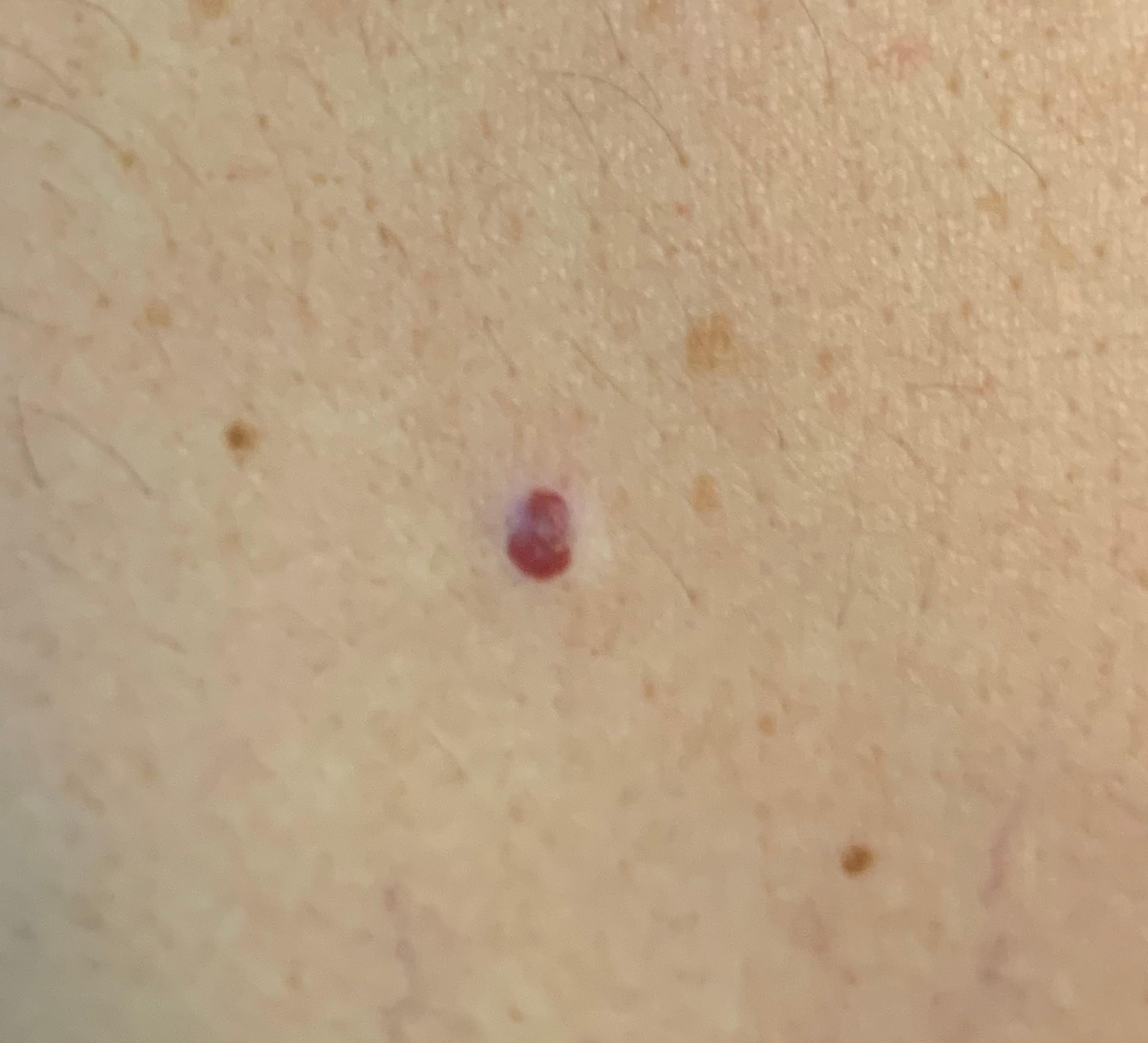Clinical context:
A wide-field clinical photograph of a skin lesion. Recorded as Fitzpatrick II. Located on the anterior trunk.
Assessment:
Clinically diagnosed as a vascular lesion.